This is a dermoscopic photograph of a skin lesion, the subject is a male aged approximately 40:
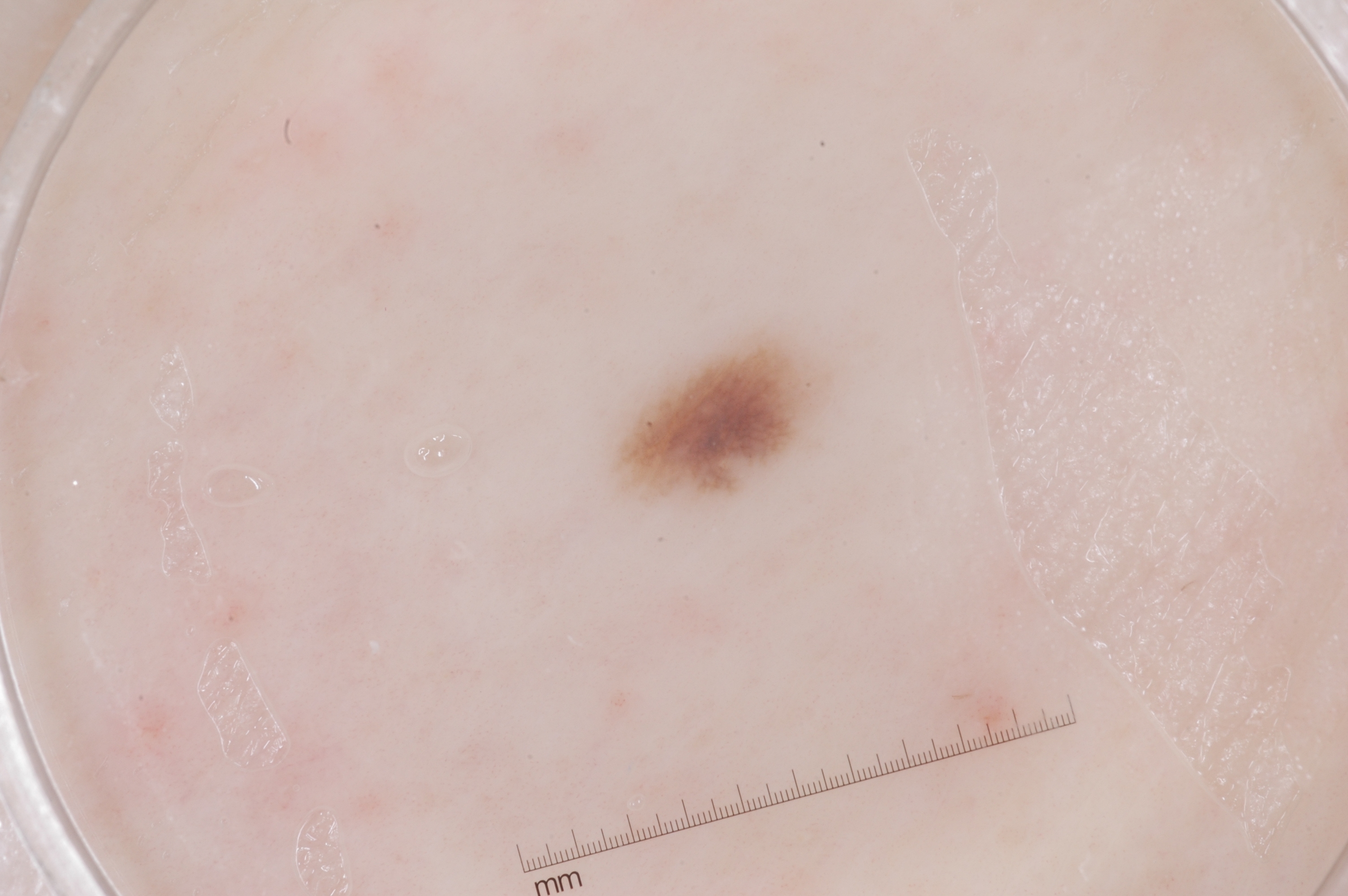{"lesion_location": {"bbox_xyxy": [622, 336, 822, 497]}, "lesion_extent": {"approx_field_fraction_pct": 2}, "dermoscopic_features": {"present": ["pigment network"], "absent": ["negative network", "milia-like cysts", "streaks"]}, "diagnosis": {"name": "melanocytic nevus", "malignancy": "benign", "lineage": "melanocytic", "provenance": "clinical"}}